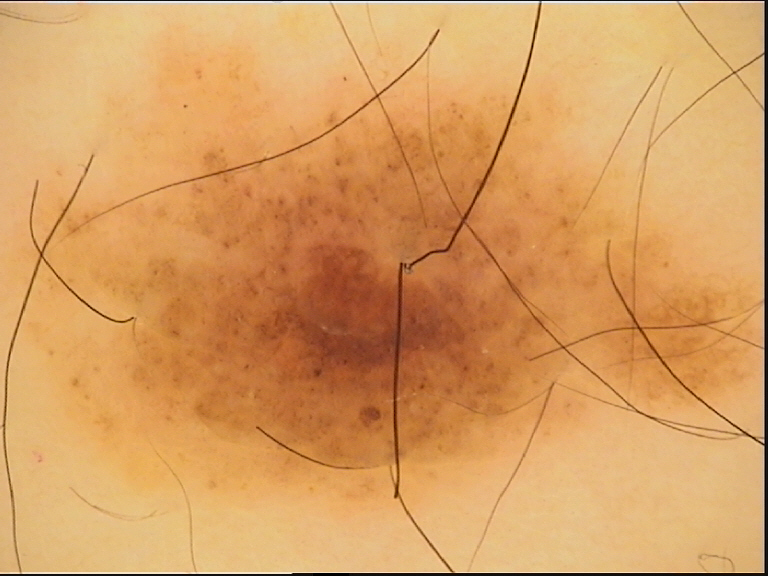The diagnosis was a dysplastic compound nevus.